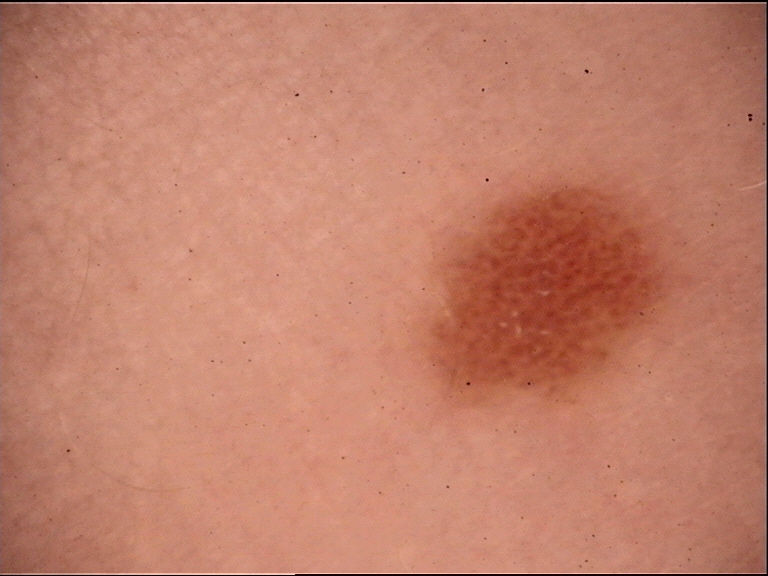A dermoscopic photograph of a skin lesion. The architecture is that of a banal lesion. Classified as a junctional nevus.